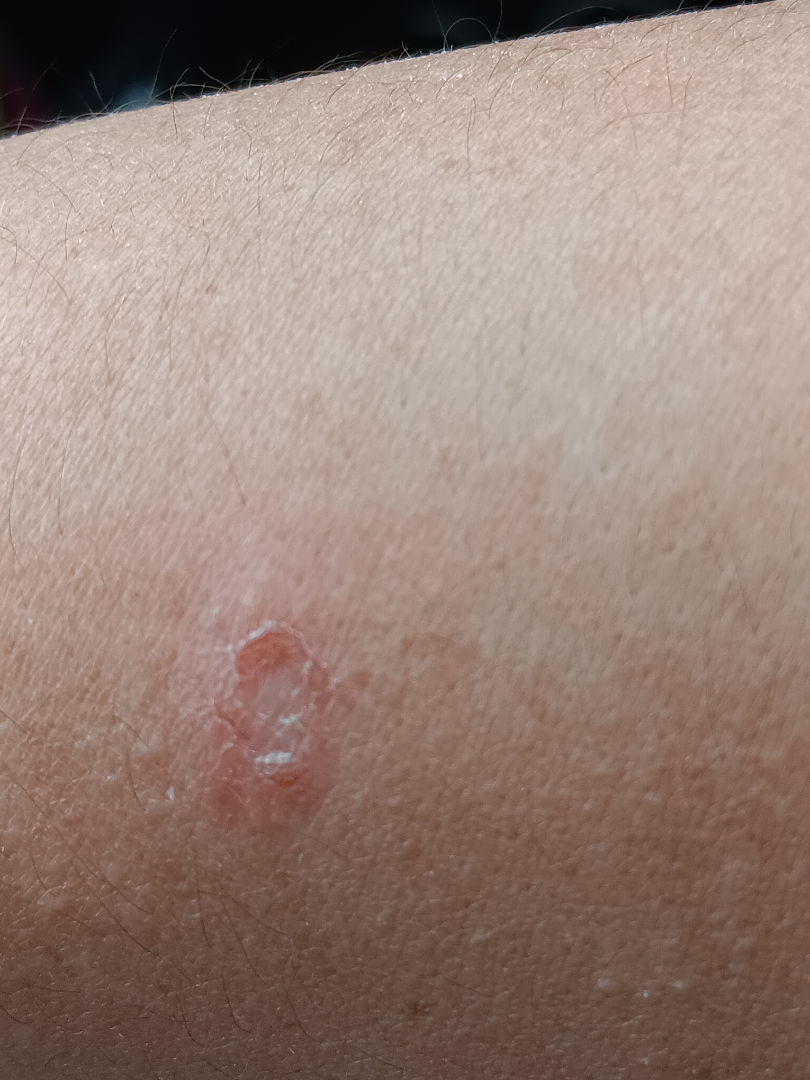The skin findings could not be characterized from the image.
The lesion is described as fluid-filled, raised or bumpy and rough or flaky.
The patient described the issue as a rash.
The patient notes the condition has been present for one to four weeks.
The patient notes itching and enlargement.
Located on the arm.
A close-up photograph.